The patient was assessed as Fitzpatrick phototype II. A female patient aged 73-77. A contact-polarized dermoscopy image of a skin lesion.
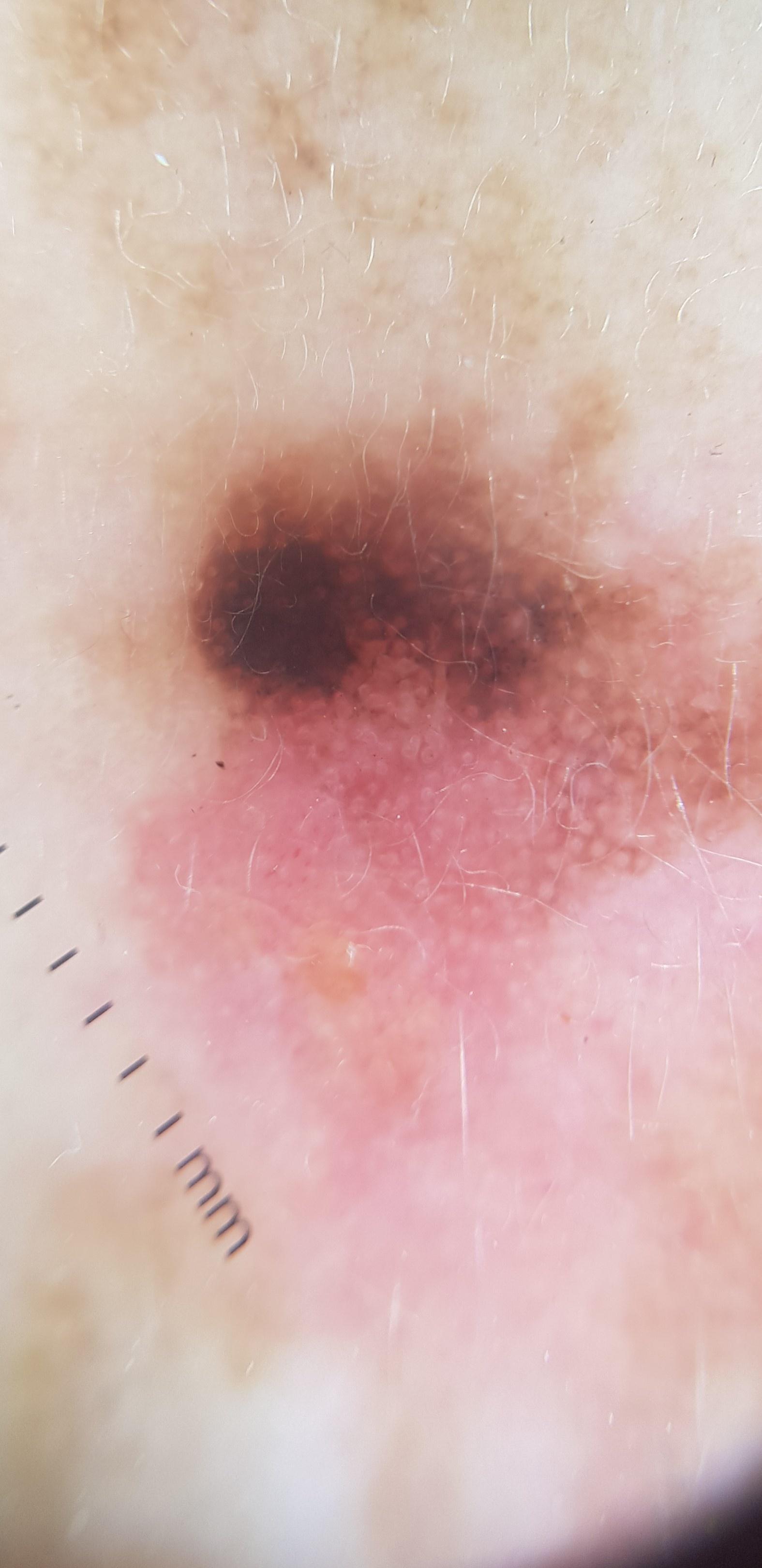body site = the head or neck | diagnosis = Melanoma (biopsy-proven).